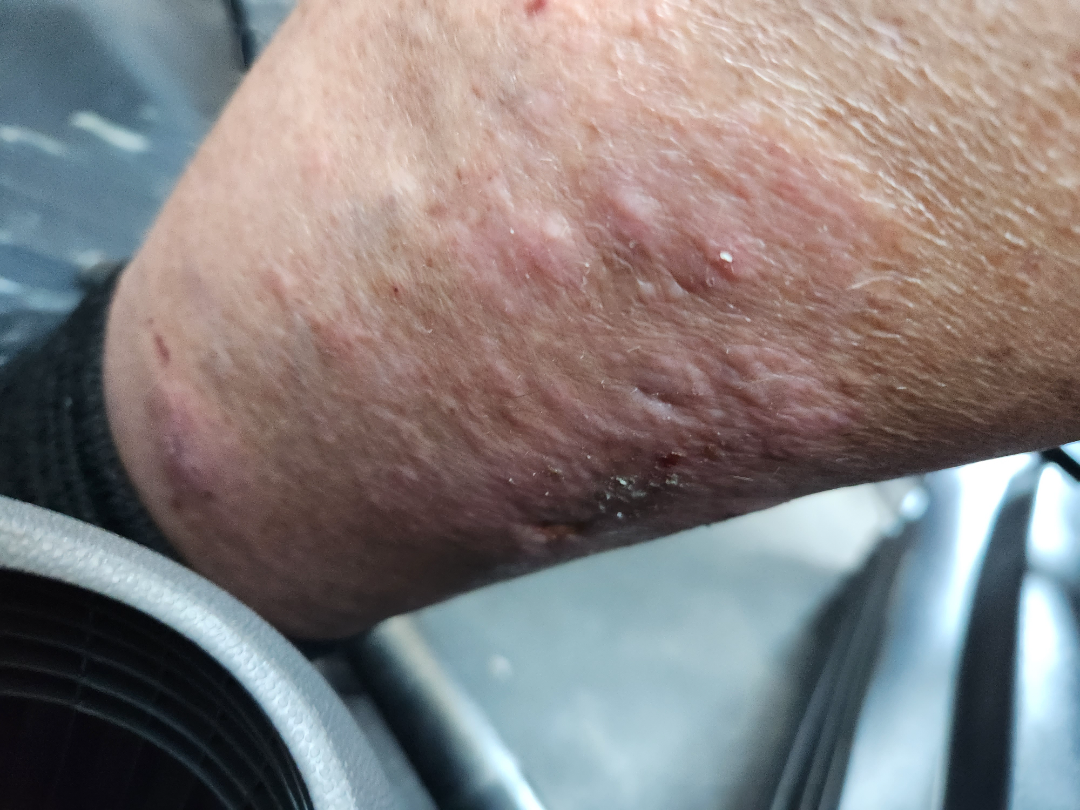differential diagnosis: Stasis Dermatitis, Psoriasis and Eczema were each considered, in no particular order